A moderate number of moles by the patient's own estimate. Dermoscopy of a skin lesion.
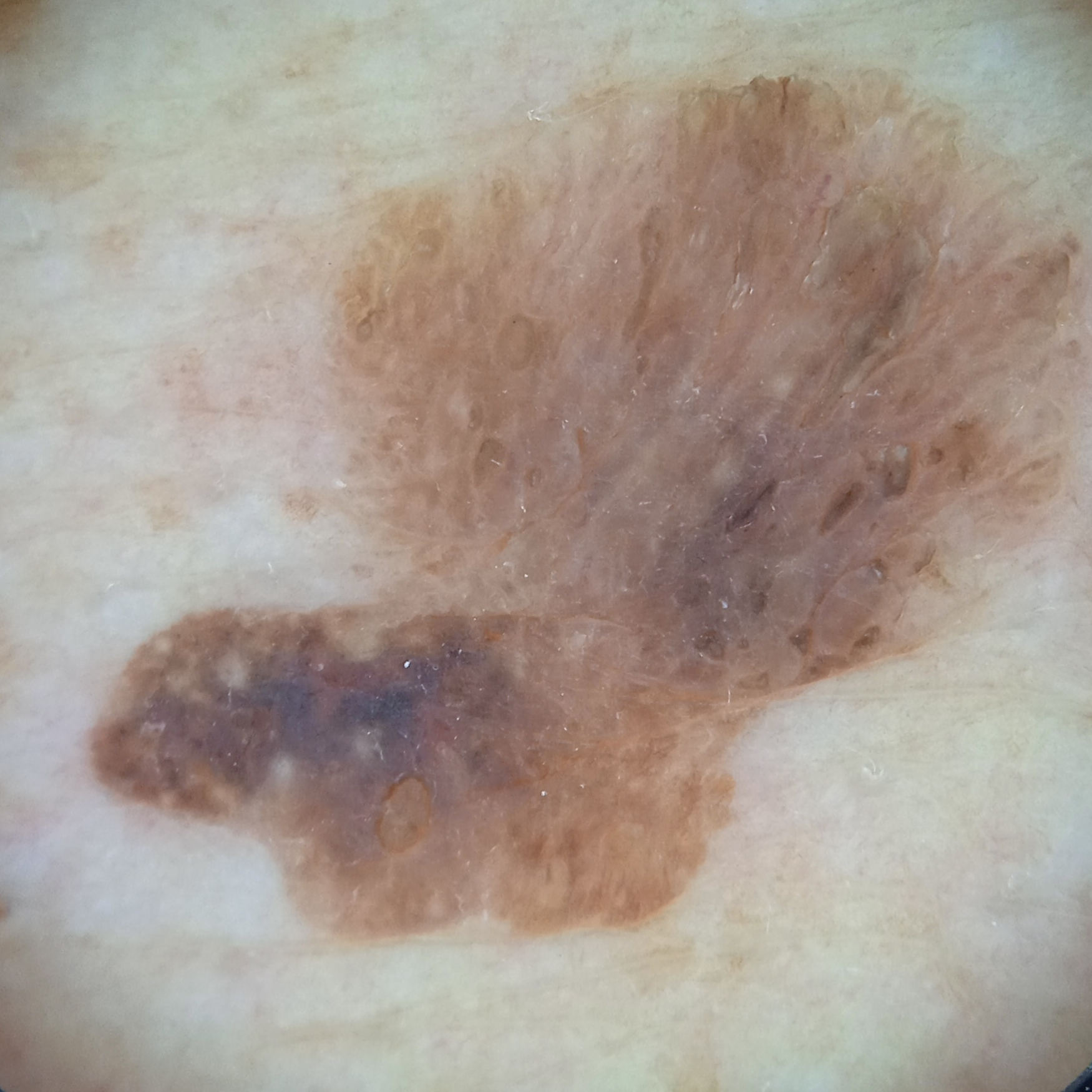Findings:
The lesion is located on the back.
Assessment:
The consensus diagnosis for this lesion was a seborrheic keratosis.